The patient reports the lesion is raised or bumpy and fluid-filled · skin tone: Fitzpatrick IV · this image was taken at an angle · the lesion involves the back of the torso and front of the torso · the patient reports the condition has been present for one to four weeks · the lesion is associated with darkening, pain, bothersome appearance and enlargement · the patient considered this a rash:
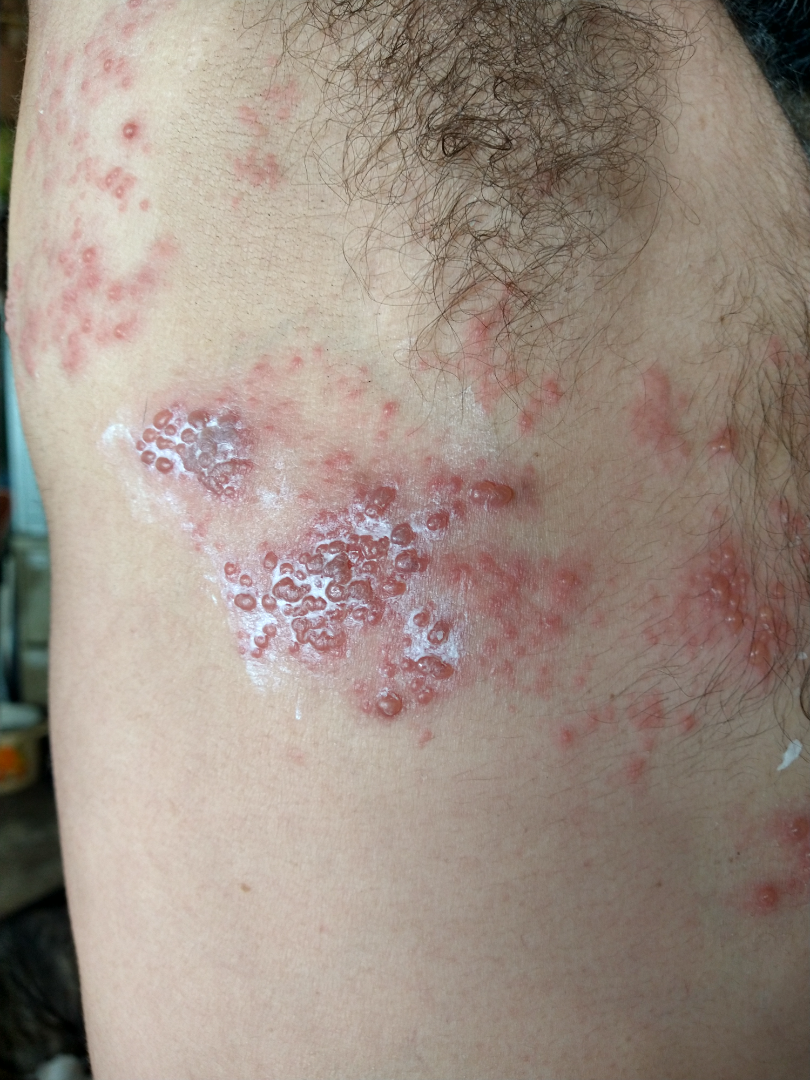Findings:
The case was difficult to assess from the available photograph.